Dermoscopy of a skin lesion.
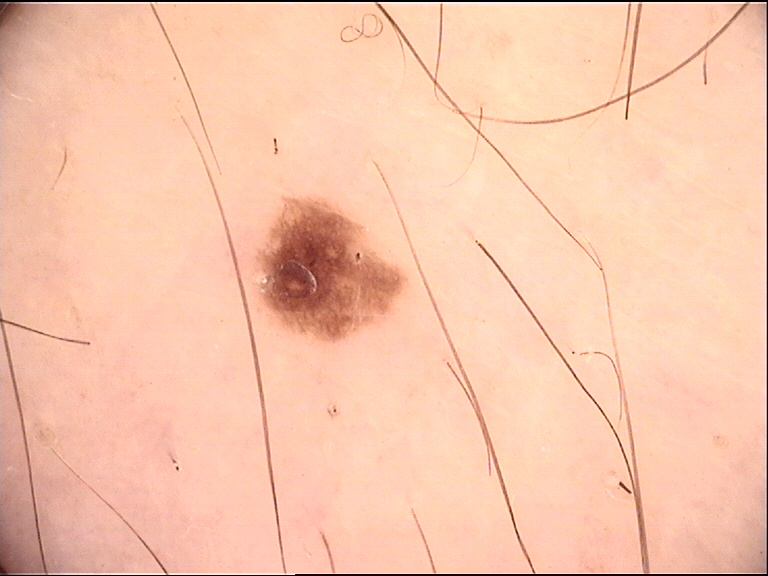Labeled as a dysplastic junctional nevus.